The photo was captured at a distance — 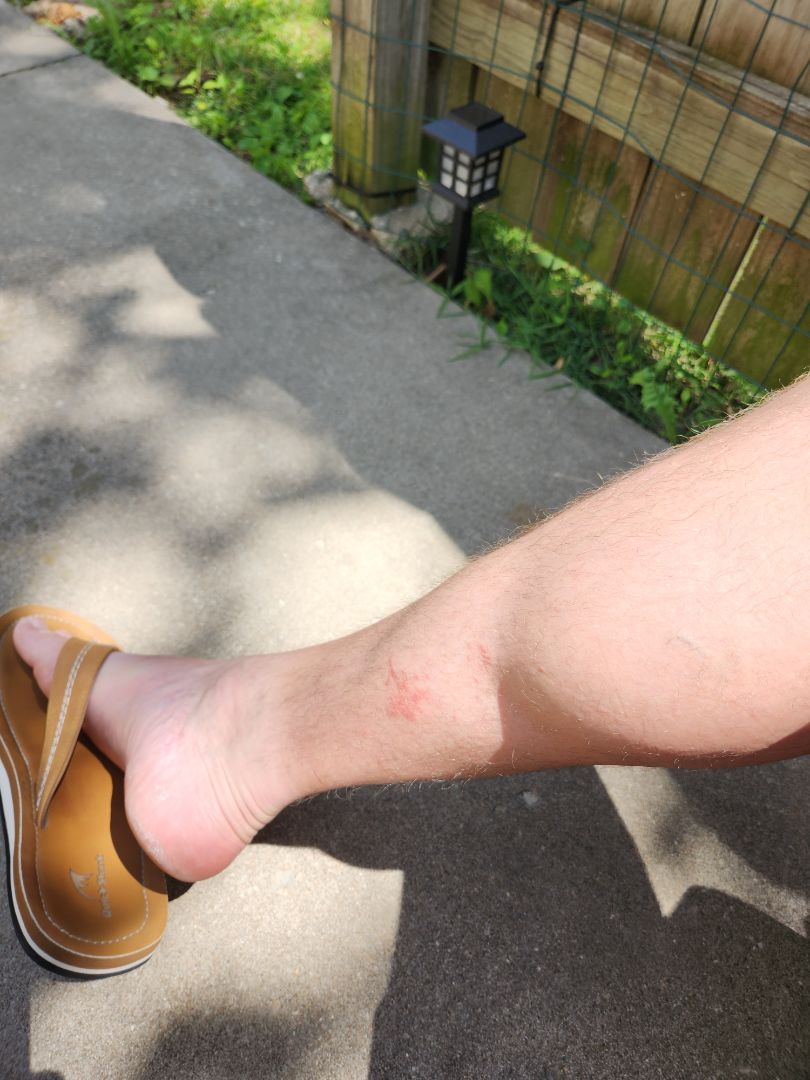Review:
The case was difficult to assess from the available photograph.